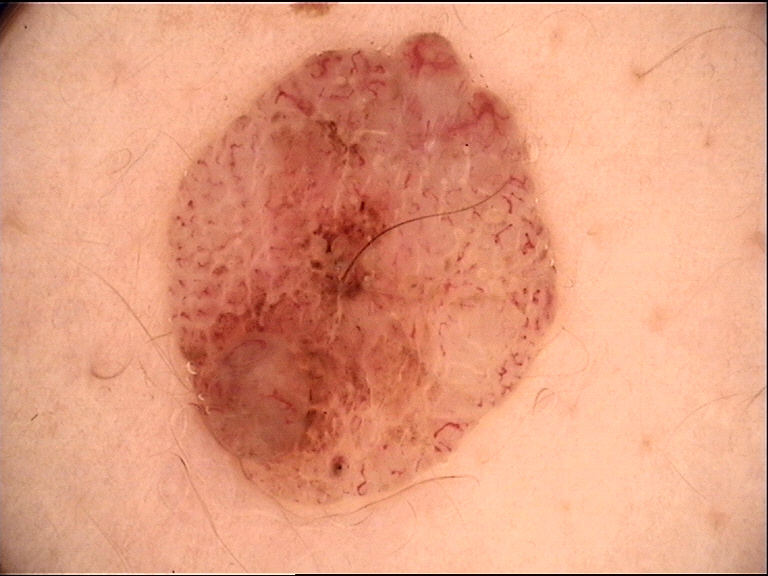Q: What kind of image is this?
A: dermatoscopy
Q: What is this lesion?
A: dermal nevus (expert consensus)